The photo was captured at an angle:
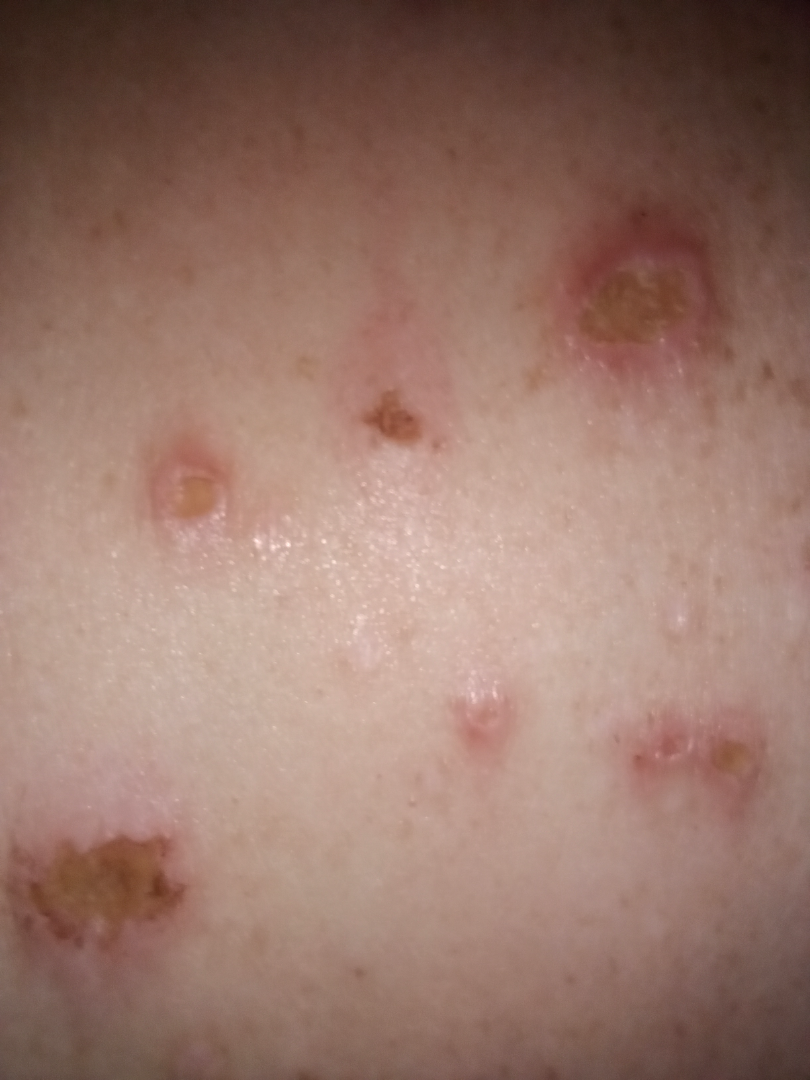skin tone: Fitzpatrick phototype IV | dermatologist impression: Folliculitis (weight 0.50); Insect Bite (weight 0.50).